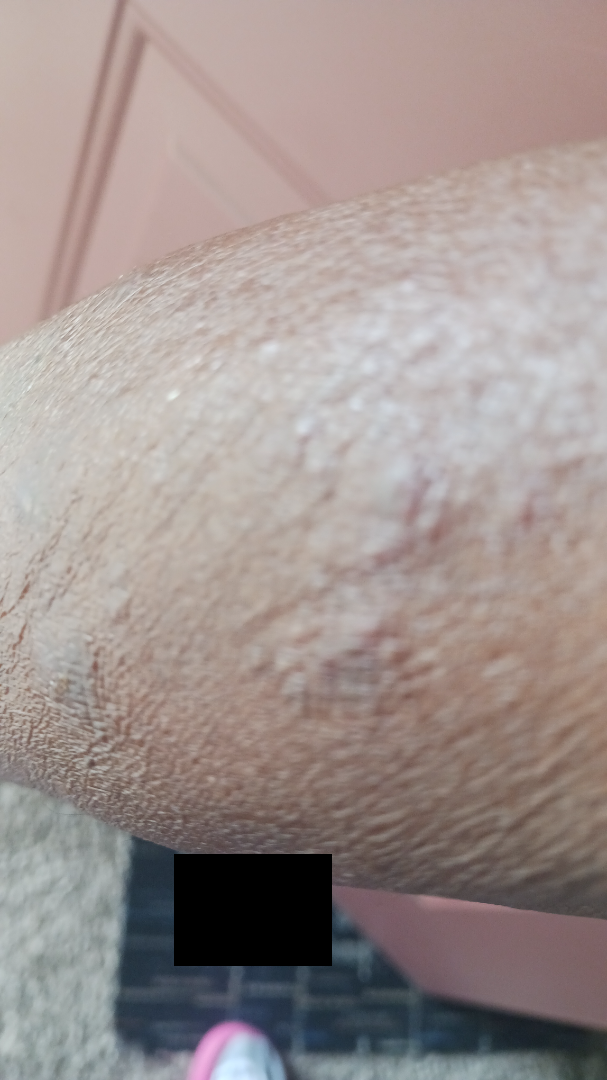assessment = ungradable on photographic review
view = at a distance
symptoms = bothersome appearance, darkening and itching
affected area = top or side of the foot, back of the hand, palm, leg and arm
history = since childhood